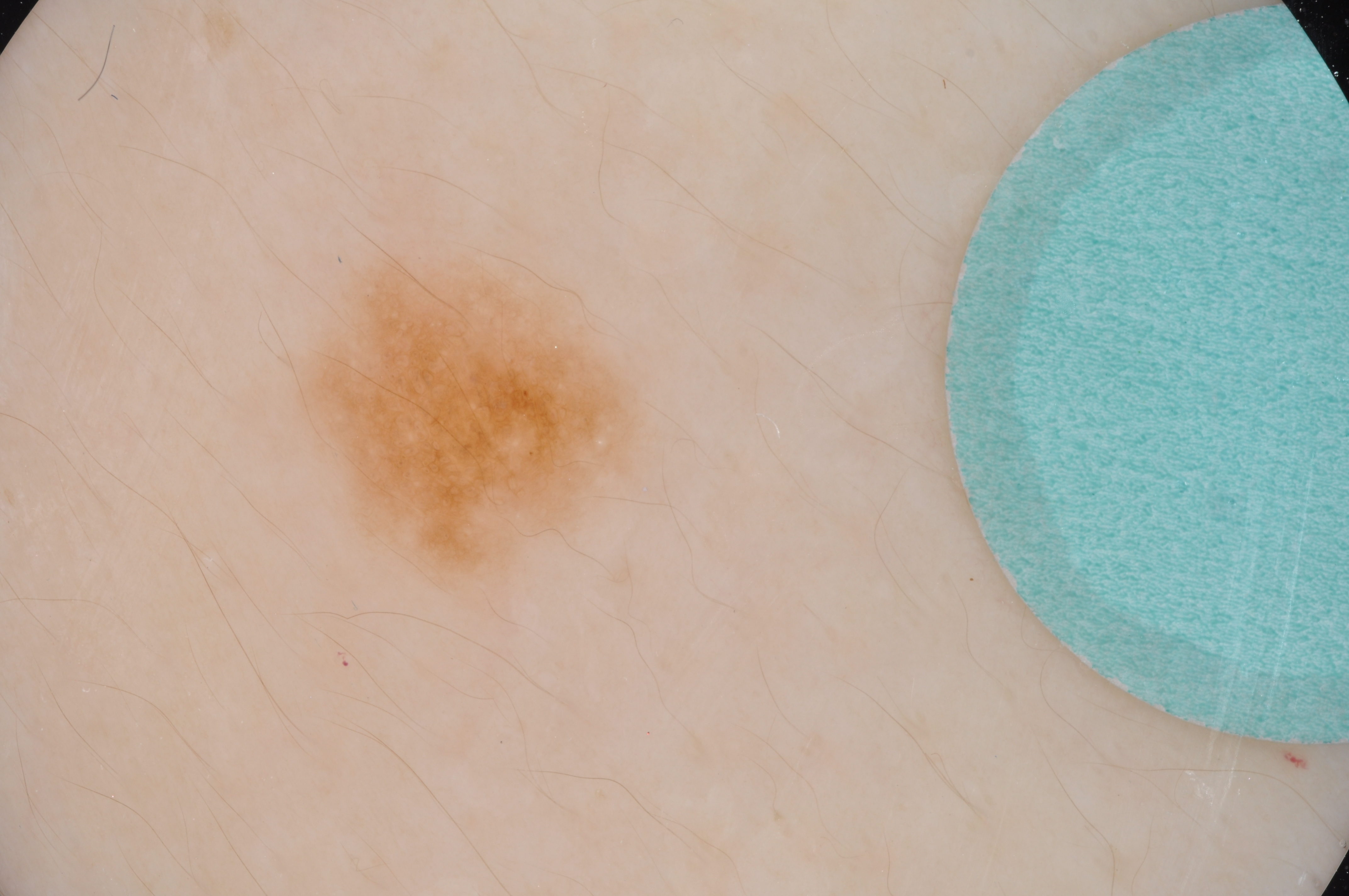A female subject, roughly 15 years of age. A dermoscopic close-up of a skin lesion. On dermoscopy, the lesion shows pigment network and milia-like cysts. The lesion occupies roughly 9% of the field. In (x1, y1, x2, y2) order, the lesion is bounded by bbox(282, 234, 659, 619). The diagnostic assessment was a melanocytic nevus.